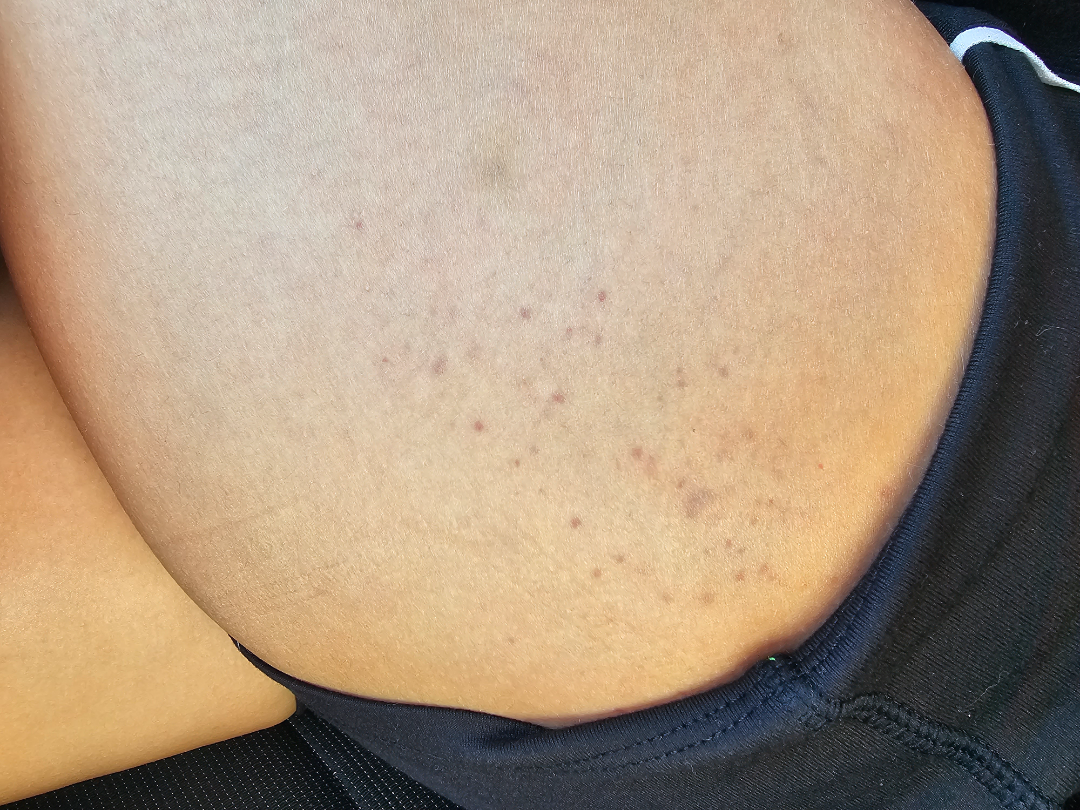  patient_category: skin that appeared healthy to them
  shot_type: close-up
  body_site:
    - leg
    - arm
  differential:
    leading:
      - Folliculitis